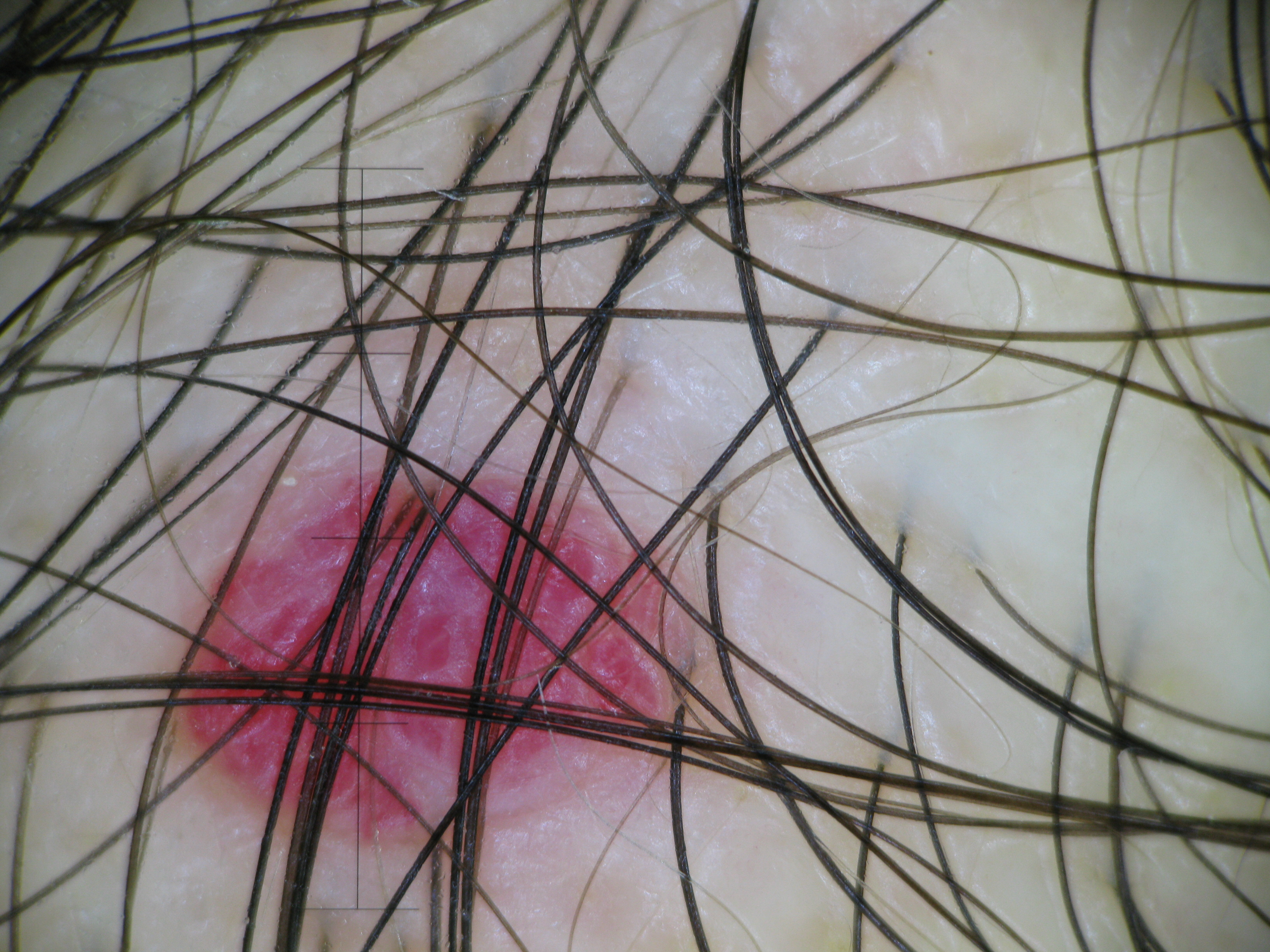classification: vascular | class: hemangioma (expert consensus).